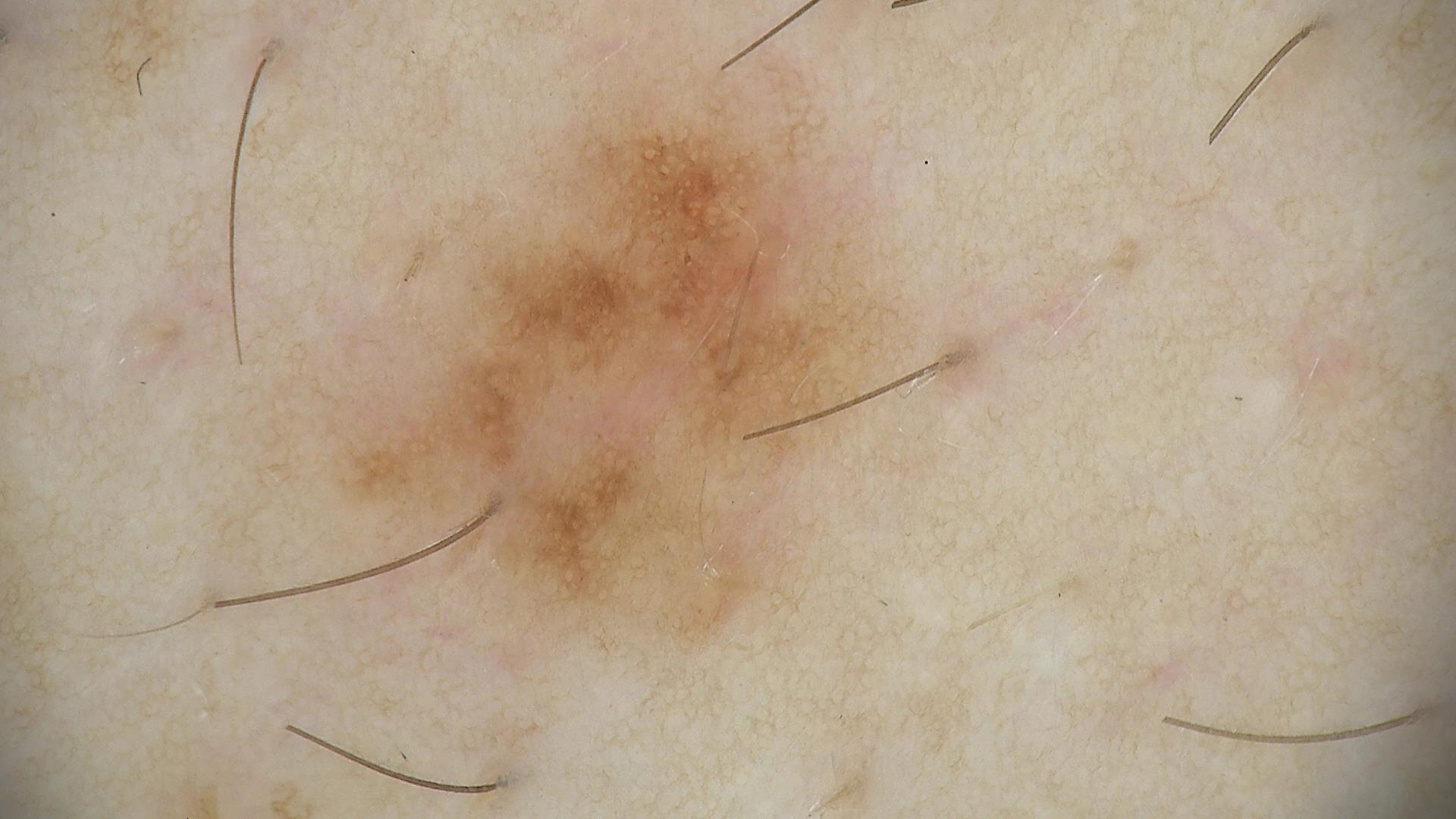Q: What is the diagnosis?
A: dysplastic junctional nevus (expert consensus)